A dermoscopic image of a skin lesion:
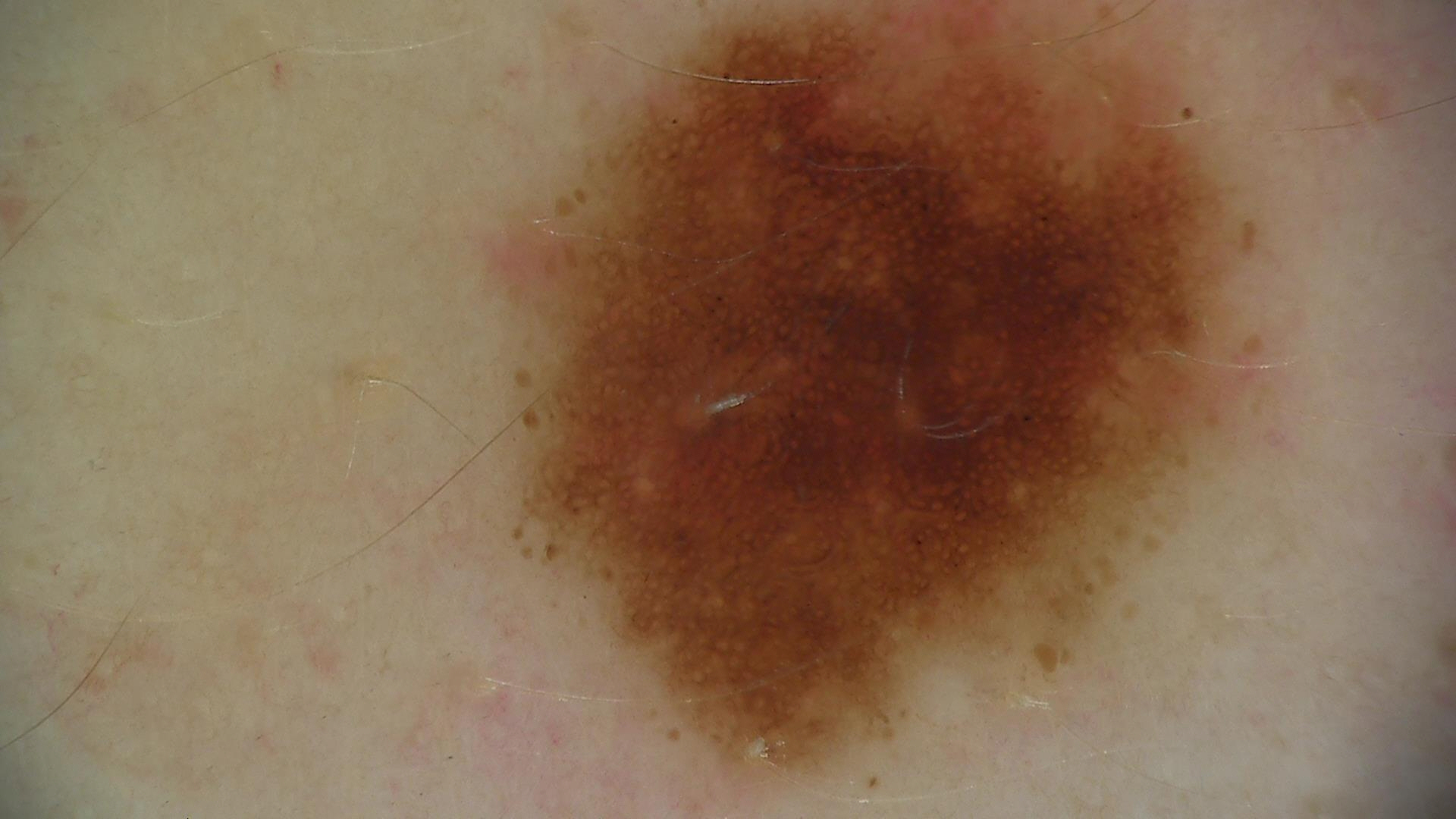assessment = dysplastic junctional nevus (expert consensus)